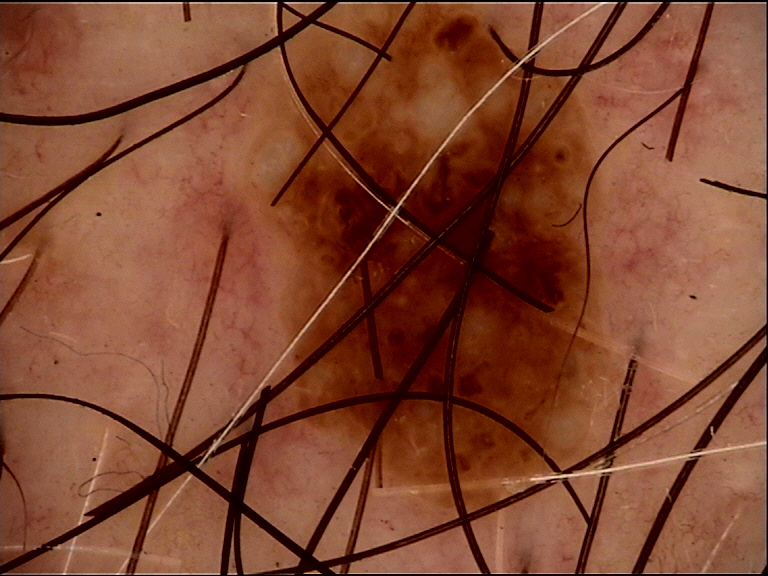{"diagnosis": {"name": "compound nevus", "code": "cb", "malignancy": "benign", "super_class": "melanocytic", "confirmation": "expert consensus"}}